A dermoscopic image of a skin lesion: 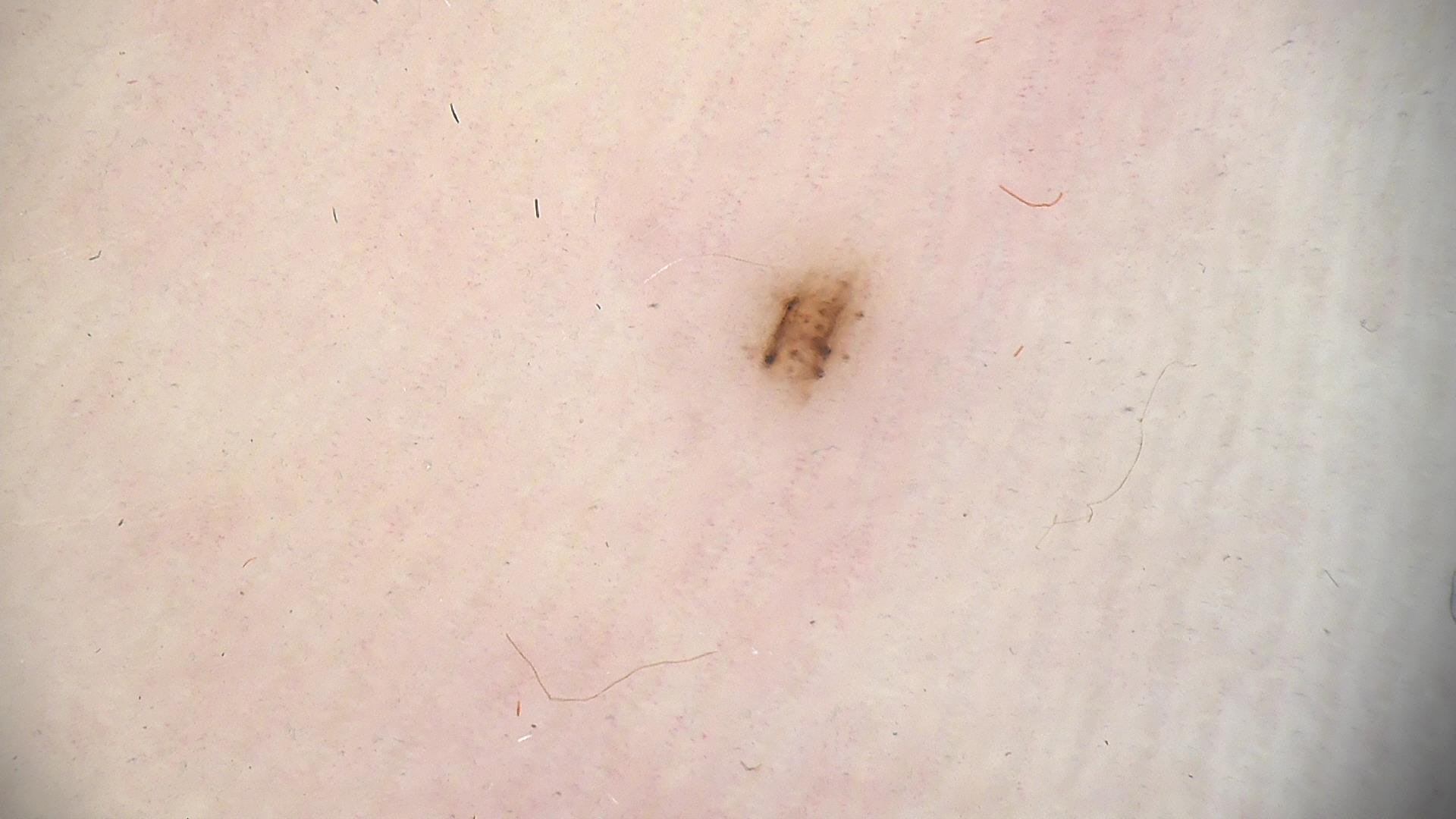class=acral dysplastic junctional nevus (expert consensus).